A dermoscopic photograph of a skin lesion.
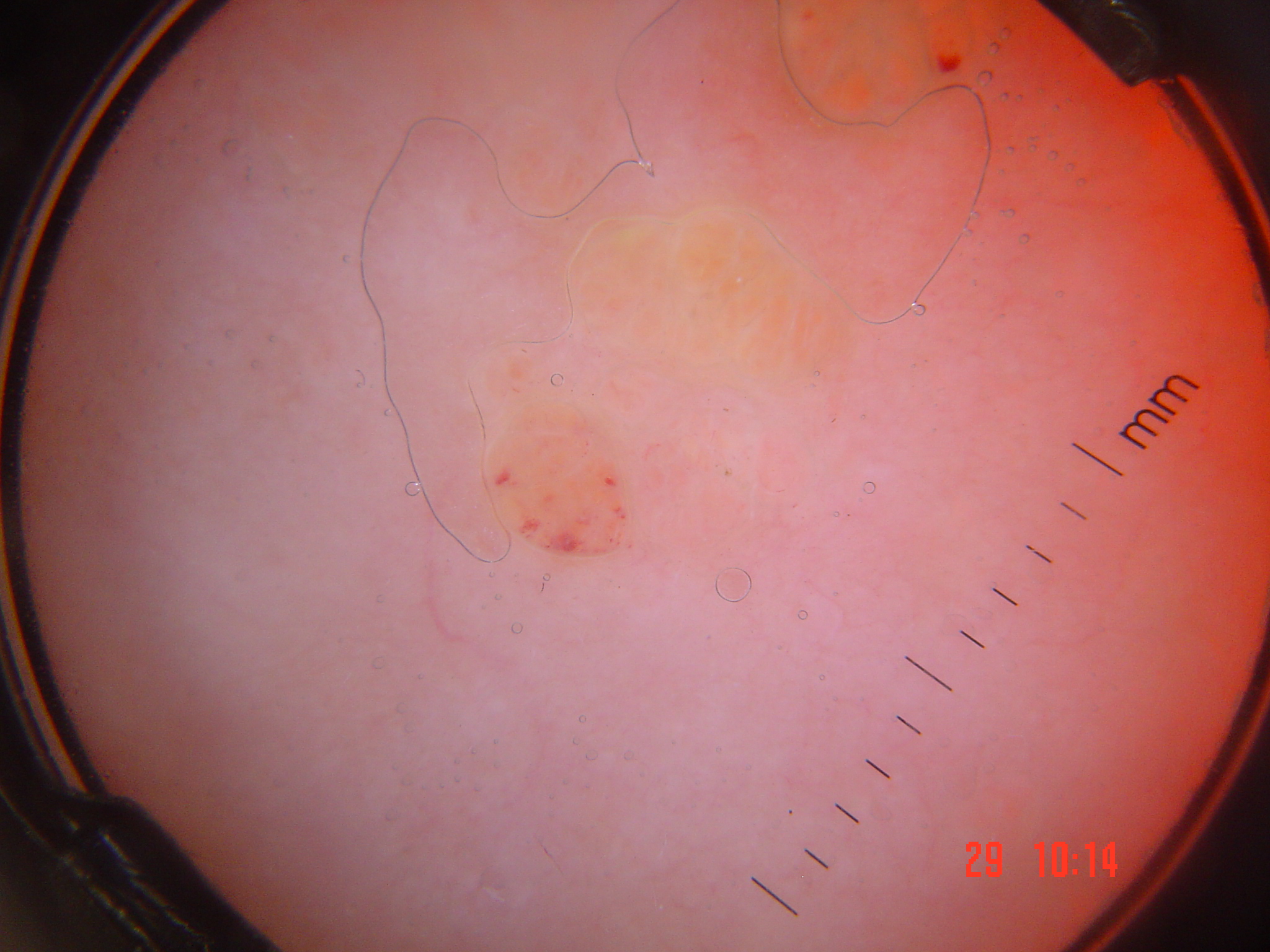Classified as a vascular, benign lesion — a lymphangioma.